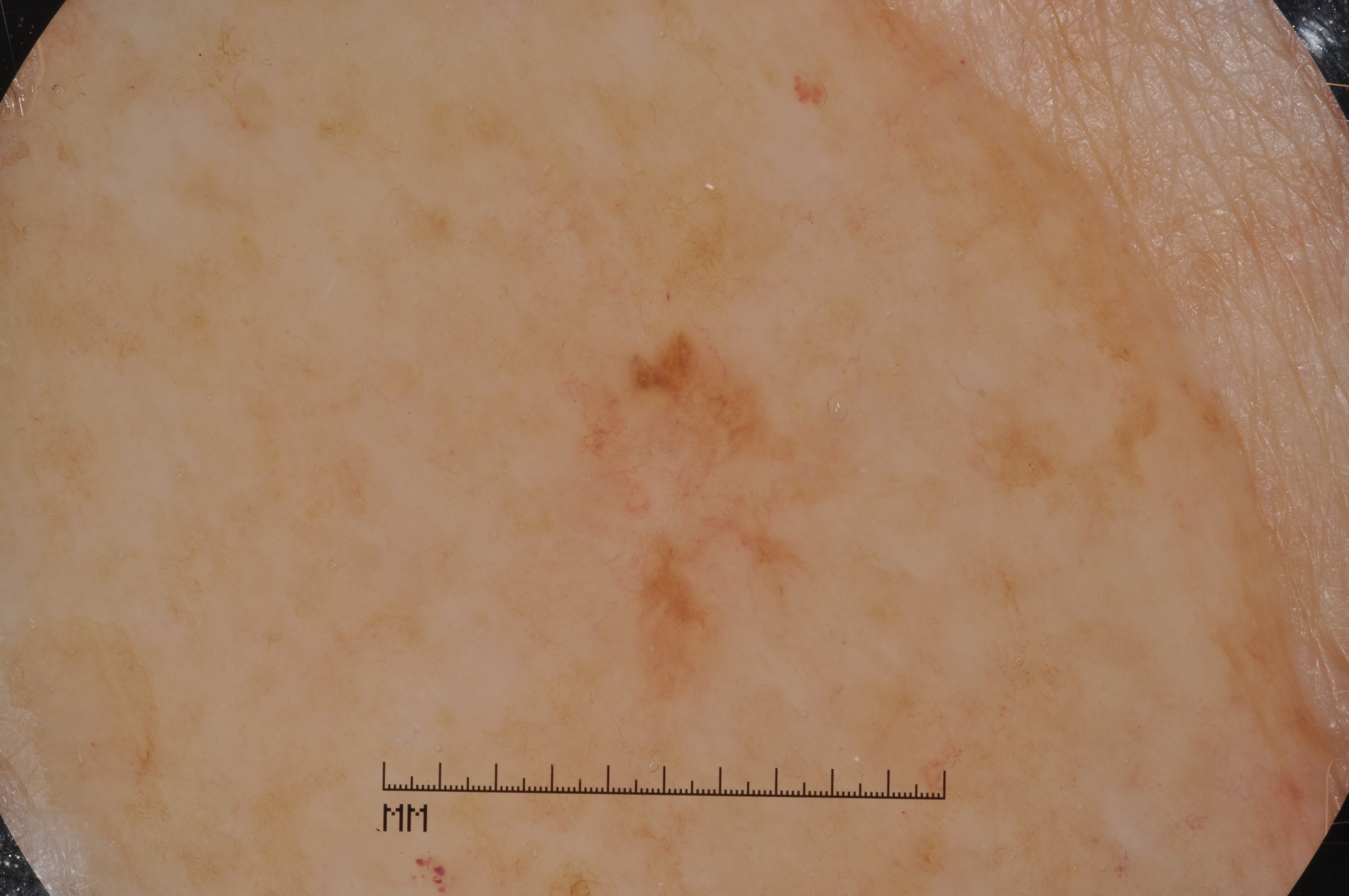Dermoscopy of a skin lesion.
The patient is a female about 80 years old.
In (x1, y1, x2, y2) order, the lesion is located at [562, 309, 854, 770].
Dermoscopy demonstrates milia-like cysts, with no negative network, streaks, or pigment network.
The lesion takes up about 4% of the image.
Confirmed on histopathology as a melanoma.